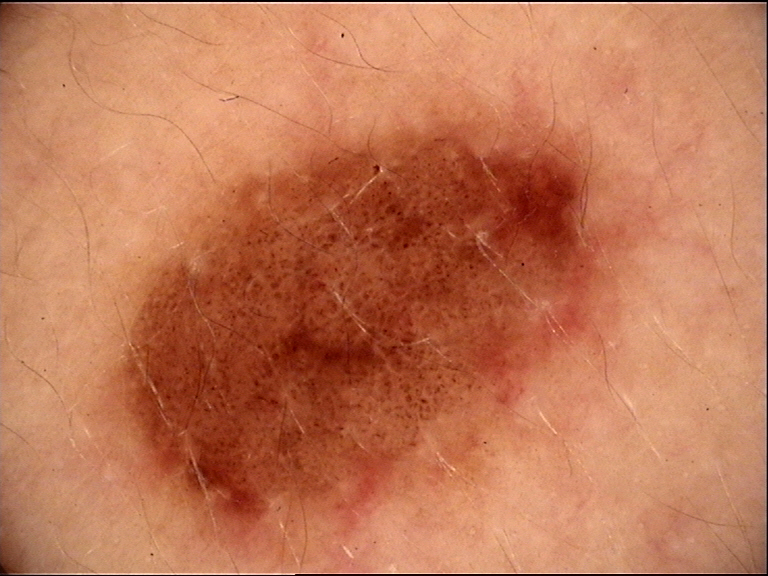diagnostic label: dysplastic junctional nevus (expert consensus).